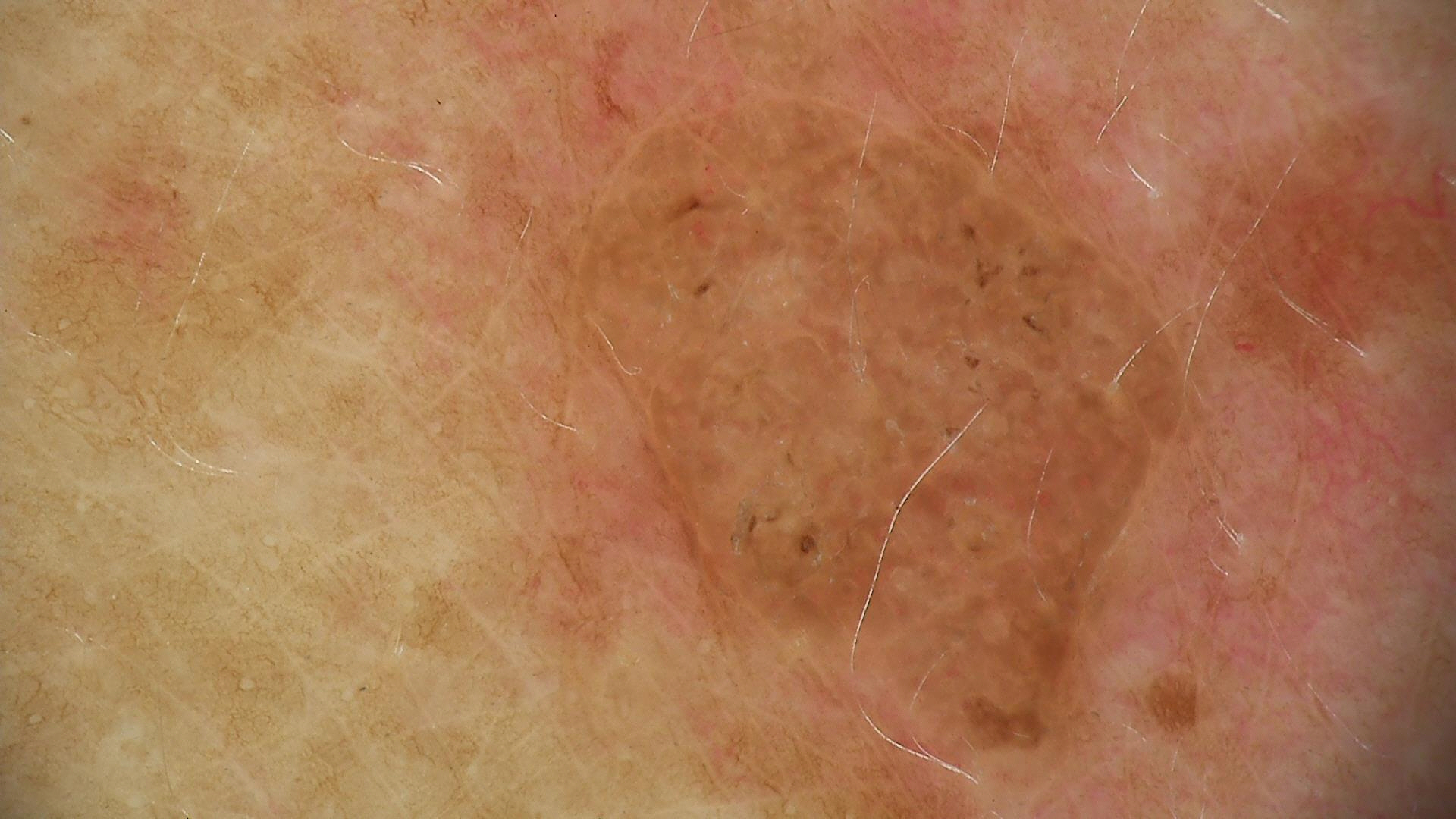Findings: A dermoscopic photograph of a skin lesion. Impression: Consistent with a keratinocytic, benign lesion — a seborrheic keratosis.